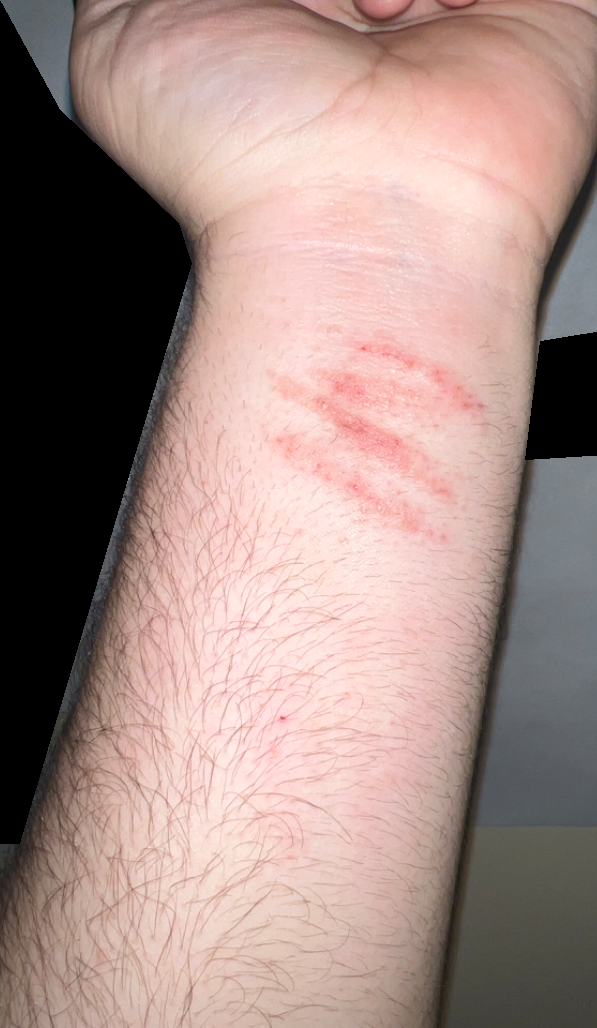Three independent reviewers: most likely Allergic Contact Dermatitis; possibly Contact dermatitis; lower on the differential is Irritant Contact Dermatitis; a remote consideration is Abrasion of wrist; less probable is Animal bite - wound.